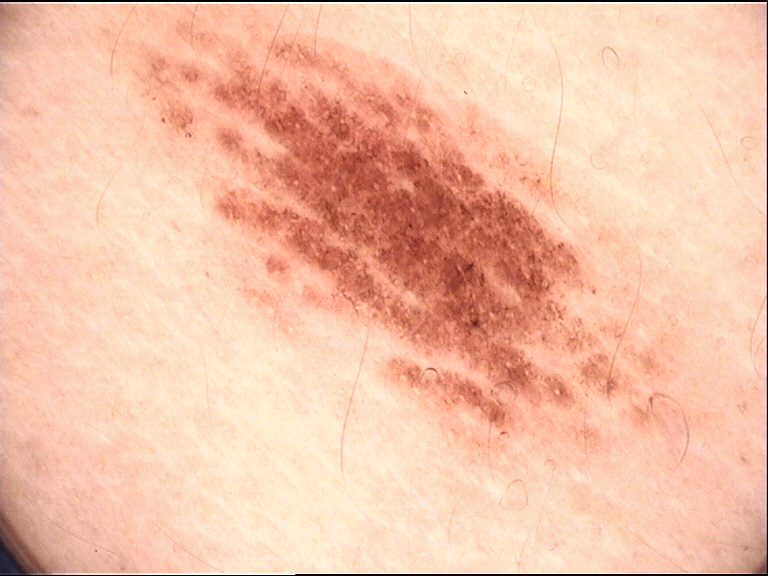A dermoscopic image of a skin lesion.
This is a banal lesion.
Consistent with a junctional nevus.